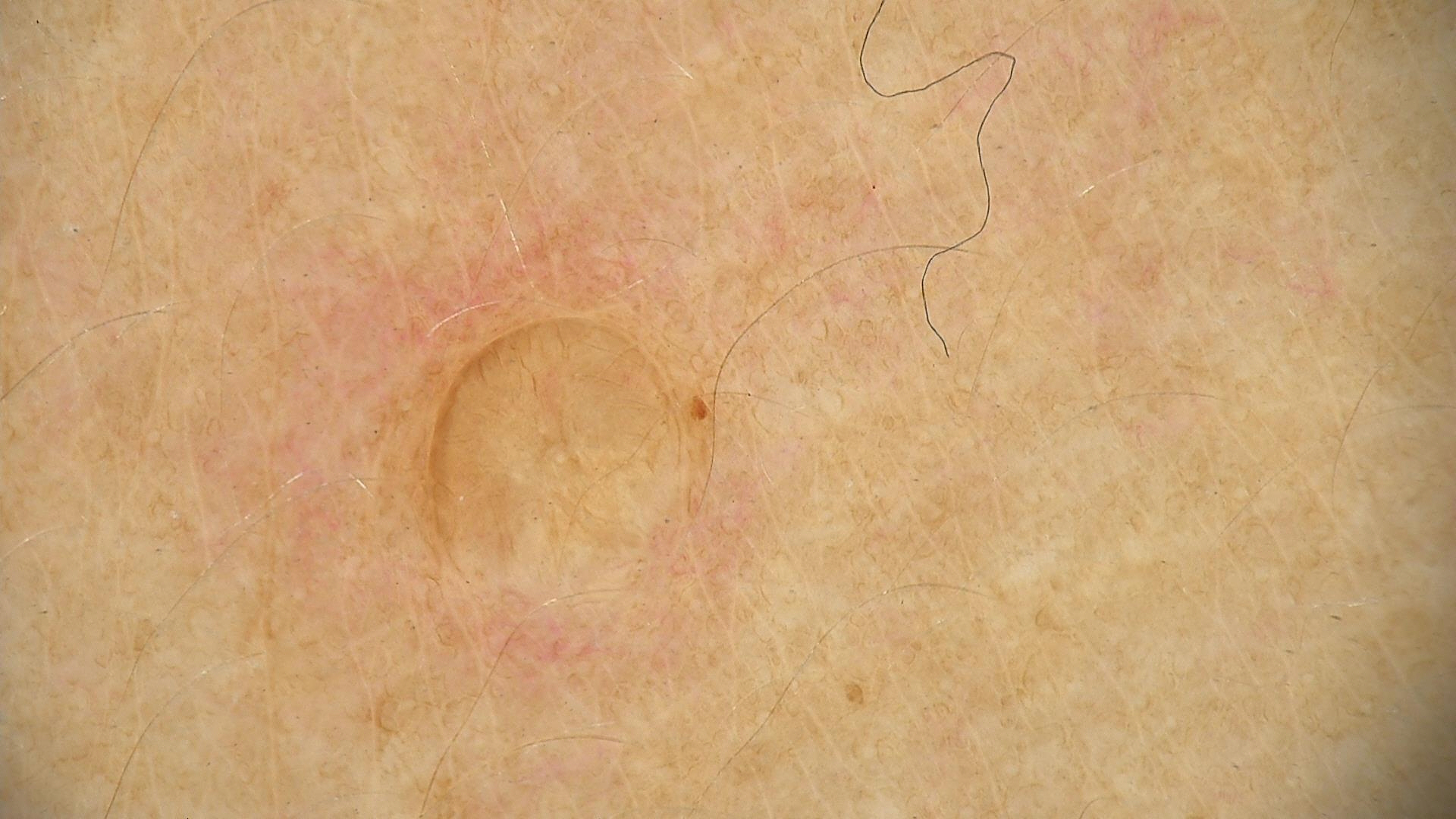Q: How is the lesion classified?
A: banal
Q: What was the diagnostic impression?
A: dermal nevus (expert consensus)